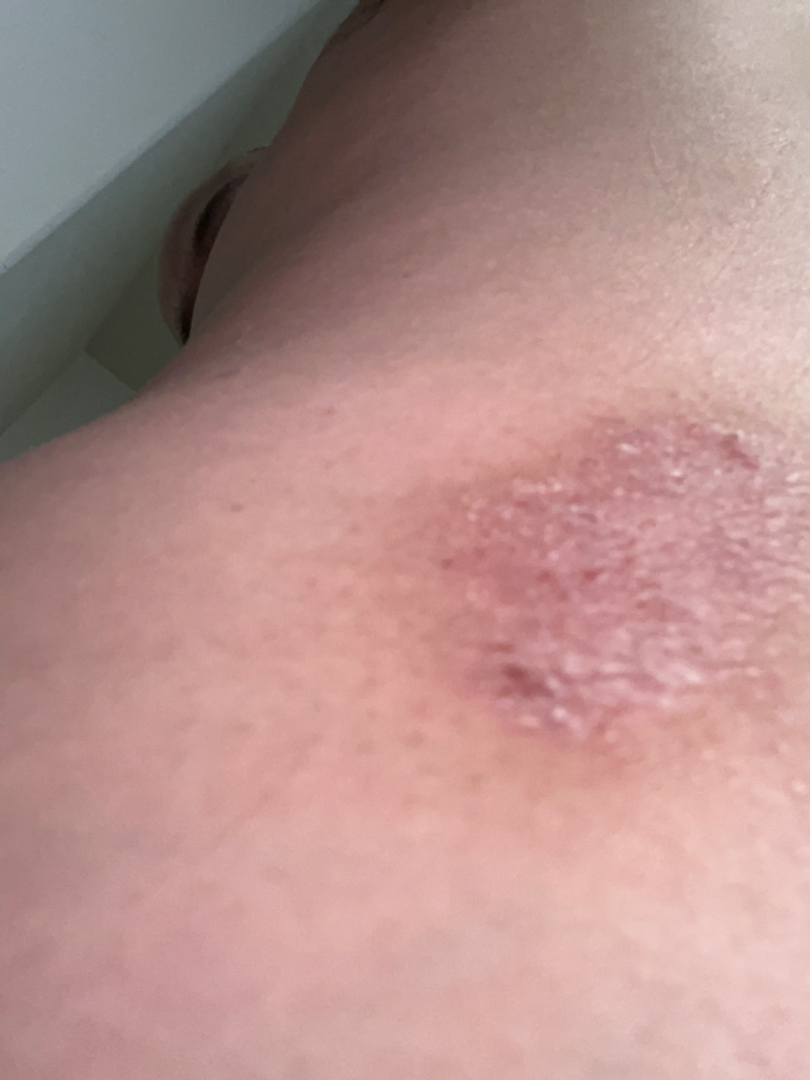Q: What was the assessment?
A: unable to determine
Q: Who is the patient?
A: male
Q: What is the framing?
A: close-up
Q: Anatomic location?
A: back of the torso